Dermoscopy of a skin lesion.
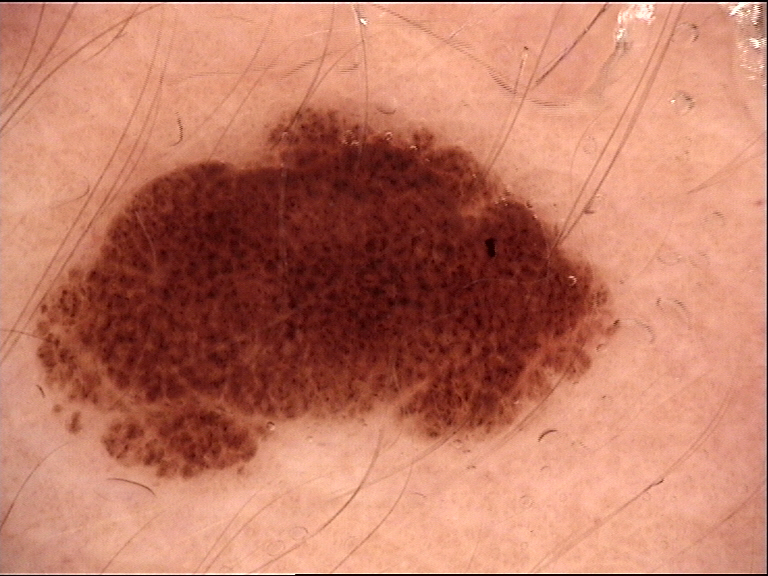Conclusion:
Diagnosed as a dysplastic compound nevus.